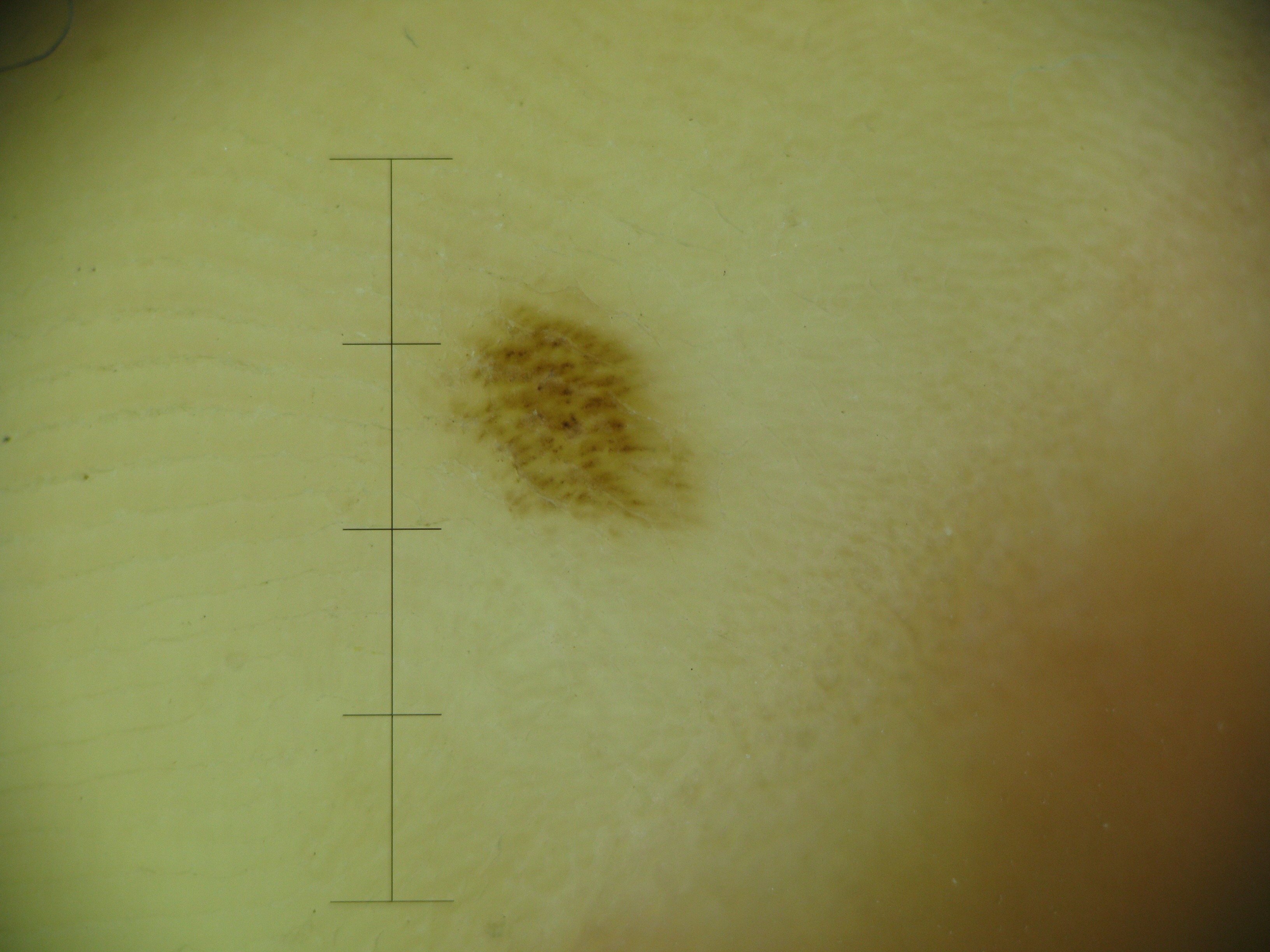  image: dermoscopy
  diagnosis:
    name: acral dysplastic junctional nevus
    code: ajd
    malignancy: benign
    super_class: melanocytic
    confirmation: expert consensus